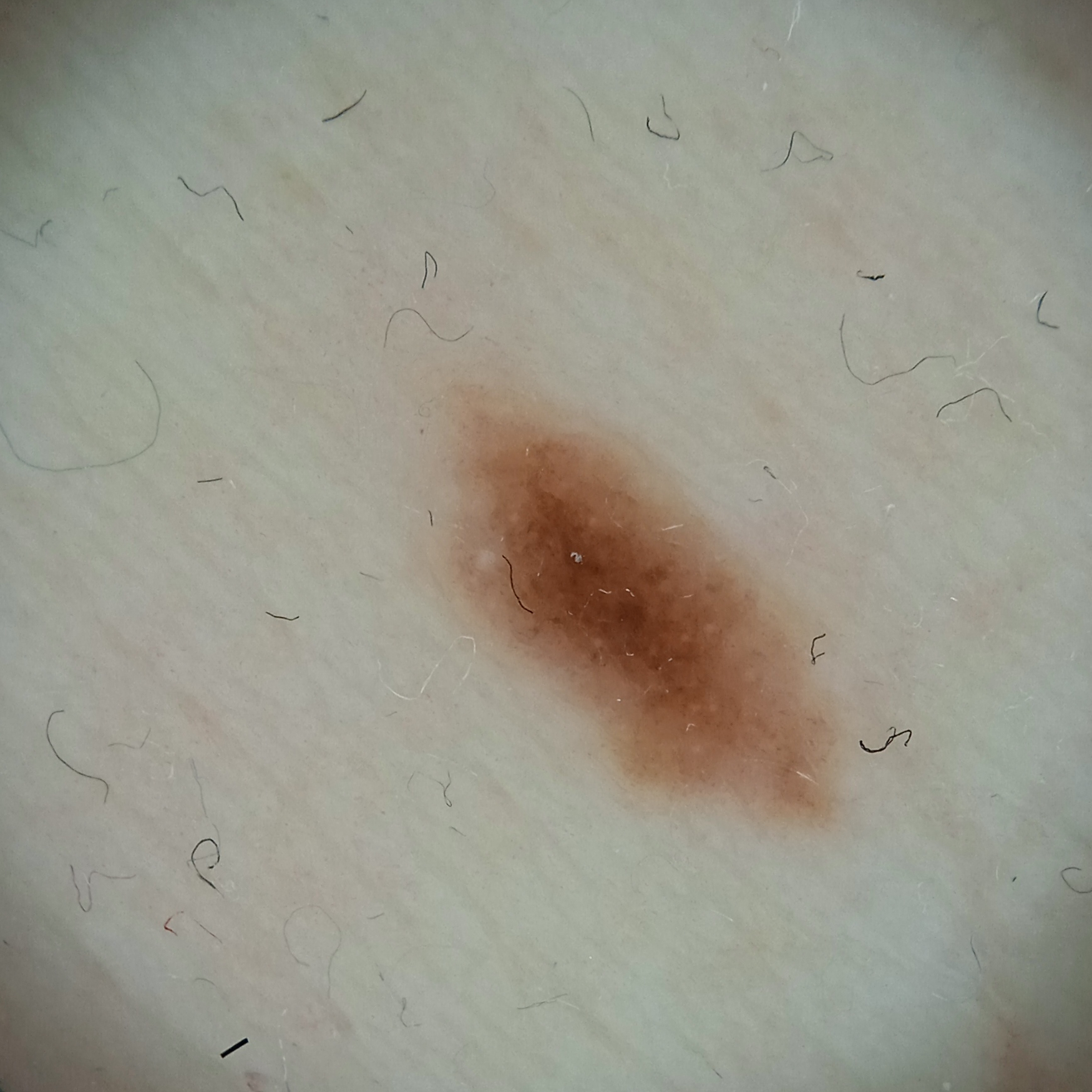Findings:
A skin lesion imaged with a dermatoscope. The patient describes having a moderate number of moles. Acquired for a research image collection, with no referral diagnosis. The lesion is located on the torso. The lesion is about 6.3 mm across.
Conclusion:
The dermatologists' assessment was a melanocytic nevus.